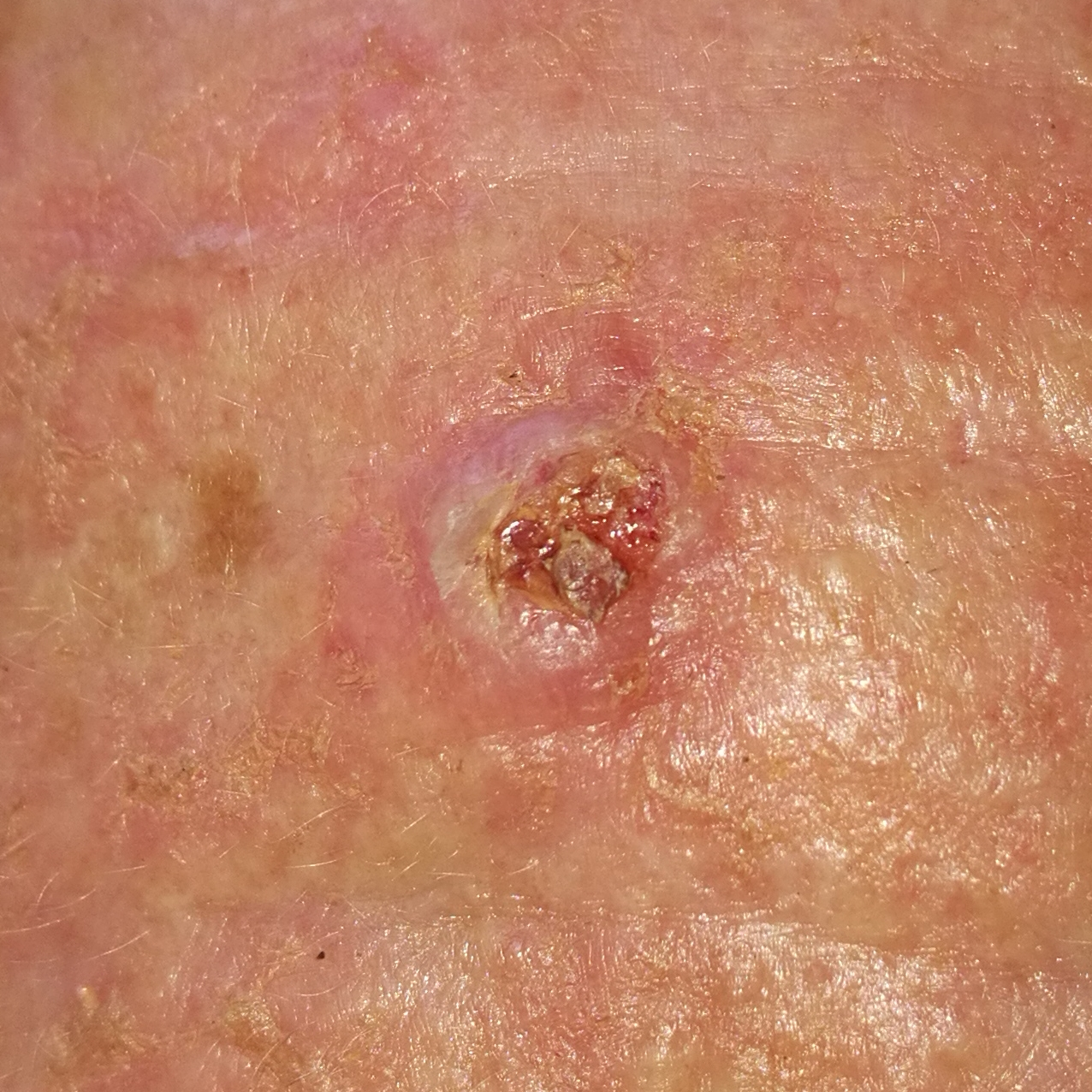Q: What does the exposure history note?
A: prior skin cancer (patient or family), prior malignancy (patient or family)
Q: Skin phototype?
A: II
Q: How was this image acquired?
A: smartphone clinical photo
Q: Where on the body is the lesion?
A: the face
Q: What symptoms does the patient report?
A: elevation, growth, pain, itching
Q: What is this lesion?
A: squamous cell carcinoma (biopsy-proven)